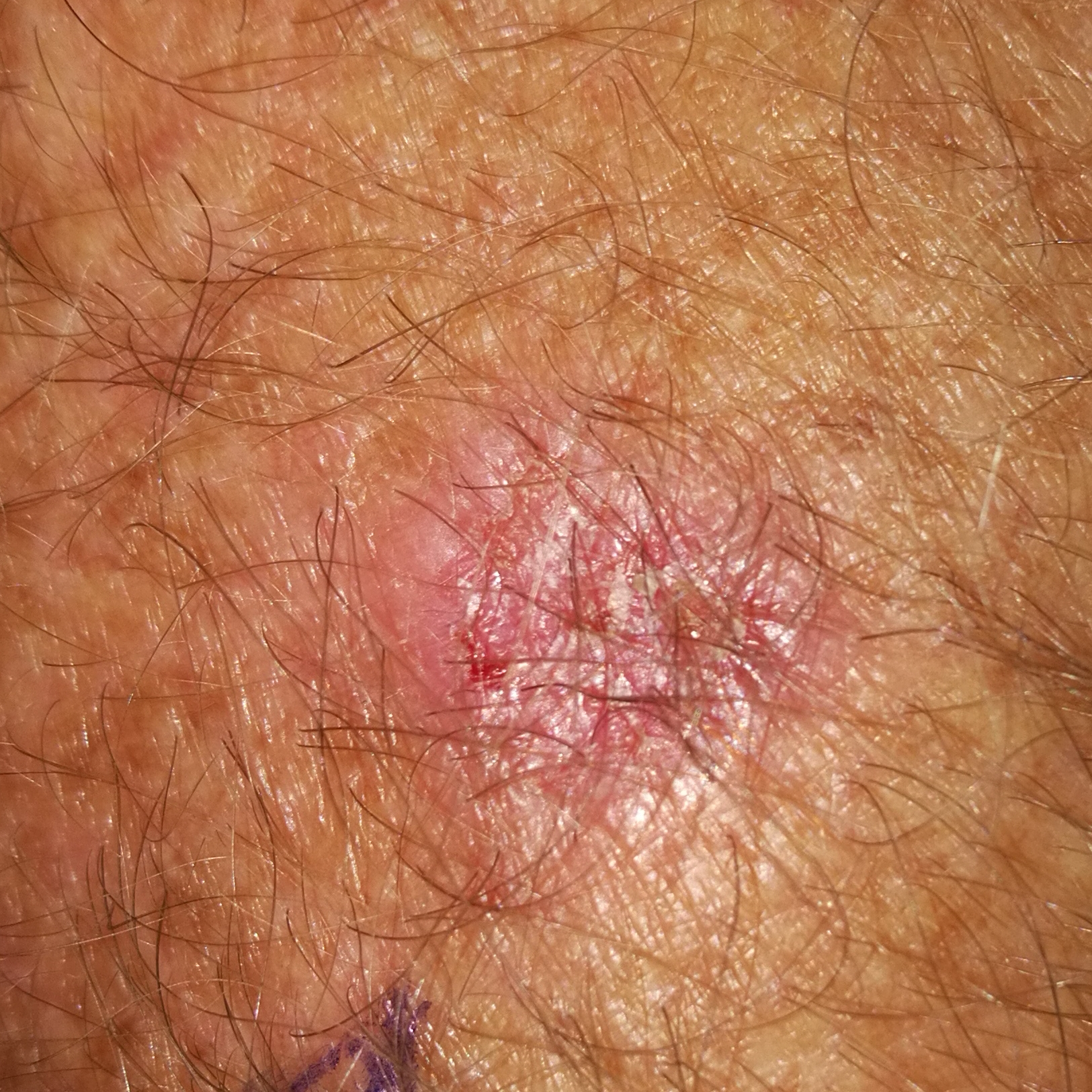| feature | finding |
|---|---|
| patient | male, in their early 50s |
| image | clinical photo |
| location | a forearm |
| patient-reported symptoms | bleeding, itching, elevation, growth |
| diagnosis | actinic keratosis (biopsy-proven) |